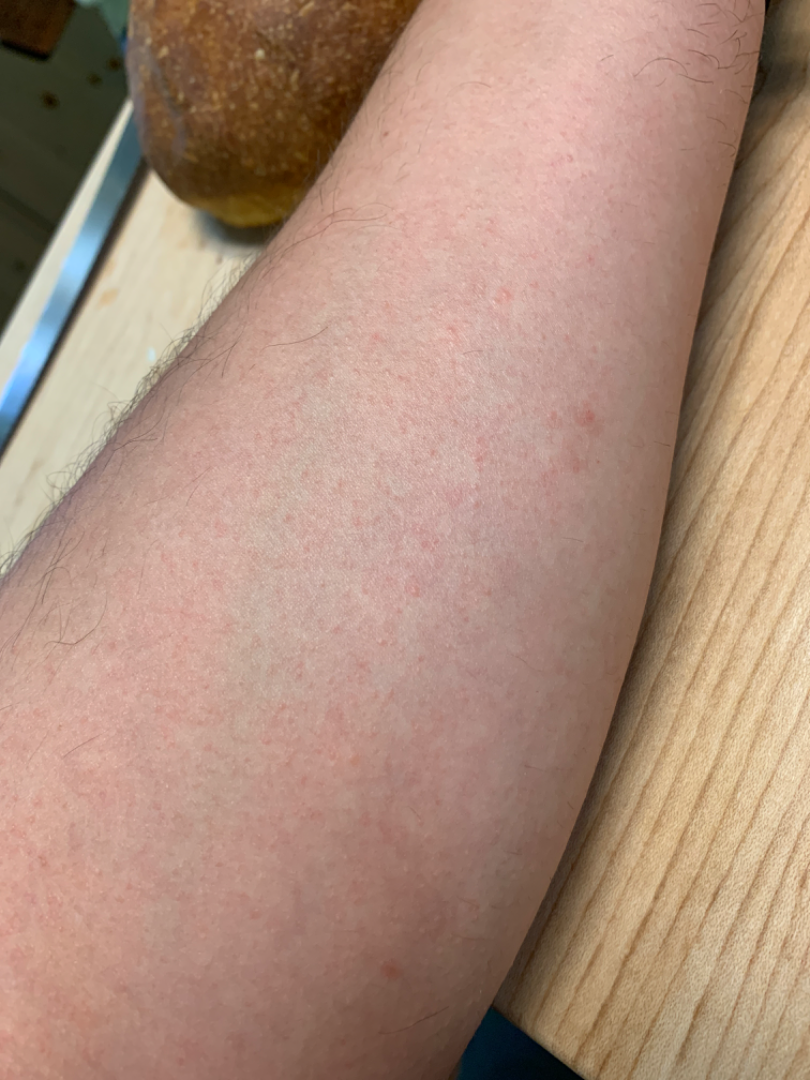patient describes the issue as=a rash
texture=raised or bumpy
subject=male, age 18–29
patient-reported symptoms=bothersome appearance
body site=arm
systemic symptoms=none reported
framing=close-up
impression=Eczema (favored); Keratosis pilaris (possible)